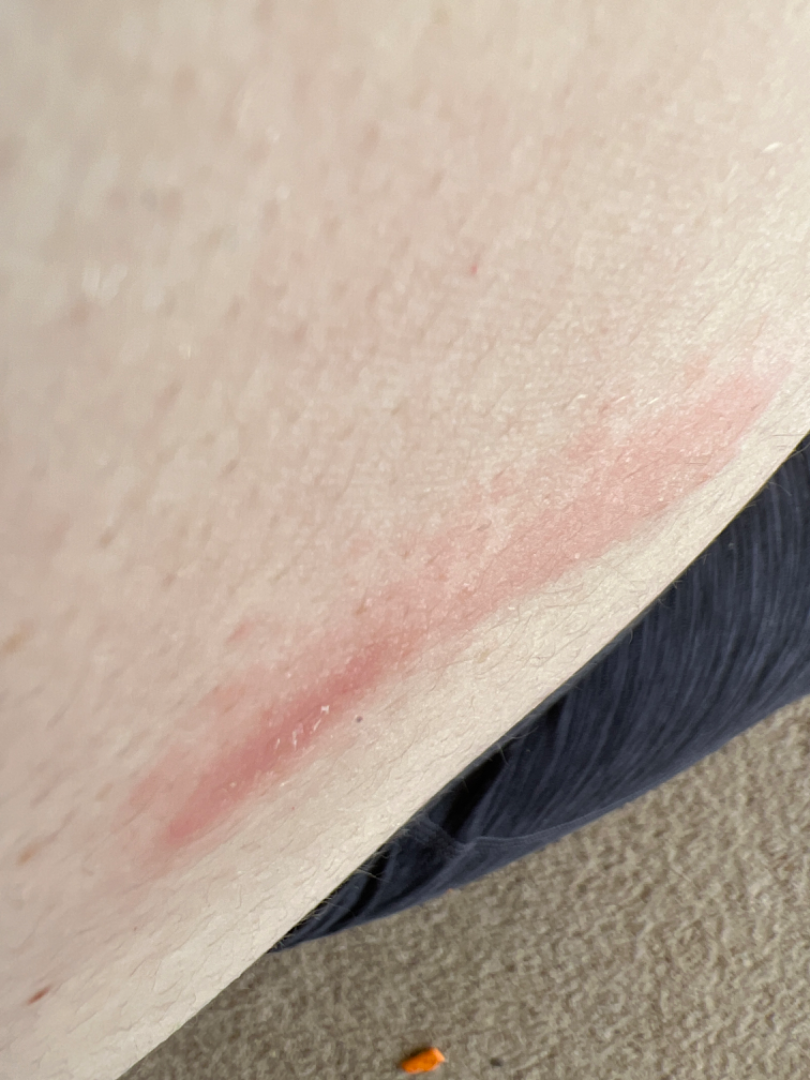Clinical context: The patient considered this a rash. The photo was captured at an angle. The contributor reports the condition has been present for one to four weeks. Reported lesion symptoms include itching and enlargement. The affected area is the front of the torso. The contributor reports the lesion is rough or flaky and raised or bumpy. The patient is a female aged 30–39. Fitzpatrick phototype I; non-clinician graders estimated 2 on the Monk skin tone scale. Assessment: Allergic Contact Dermatitis (weight 0.37); Contact dermatitis (weight 0.23); Acute dermatitis, NOS (weight 0.14); Irritant Contact Dermatitis (weight 0.14); Urticaria (weight 0.12).